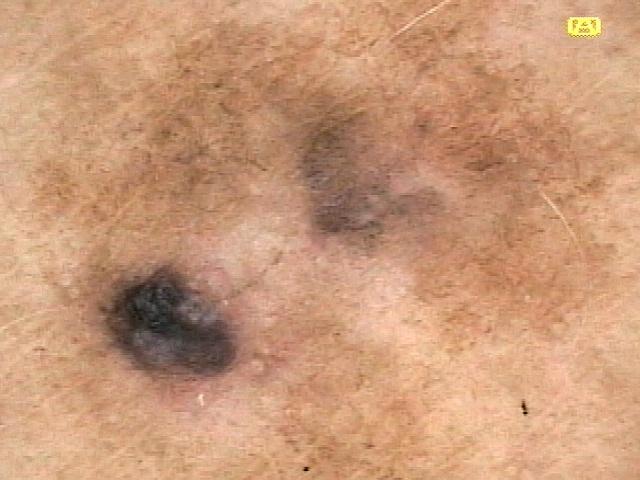A female subject roughly 65 years of age.
Fitzpatrick phototype II.
The lesion is on an upper extremity.
Biopsy-confirmed as a malignancy — a melanoma.